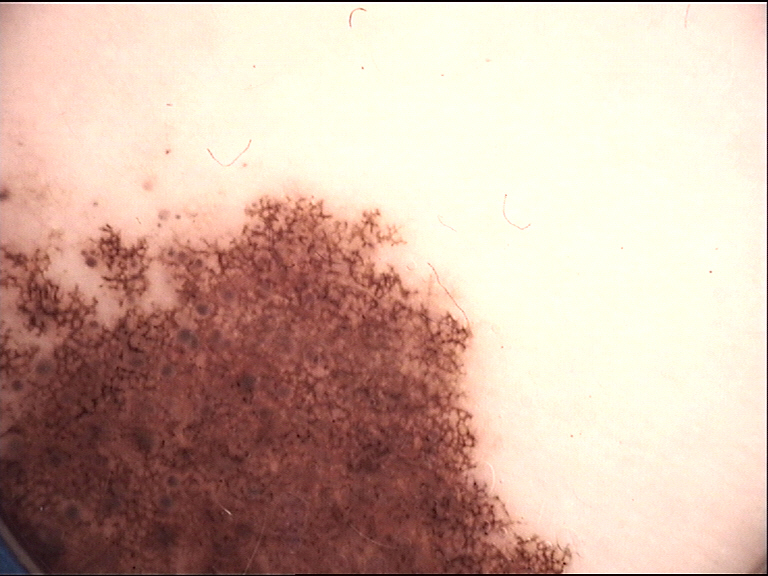Q: What is the diagnosis?
A: congenital compound nevus (expert consensus)